A dermatoscopic image of a skin lesion.
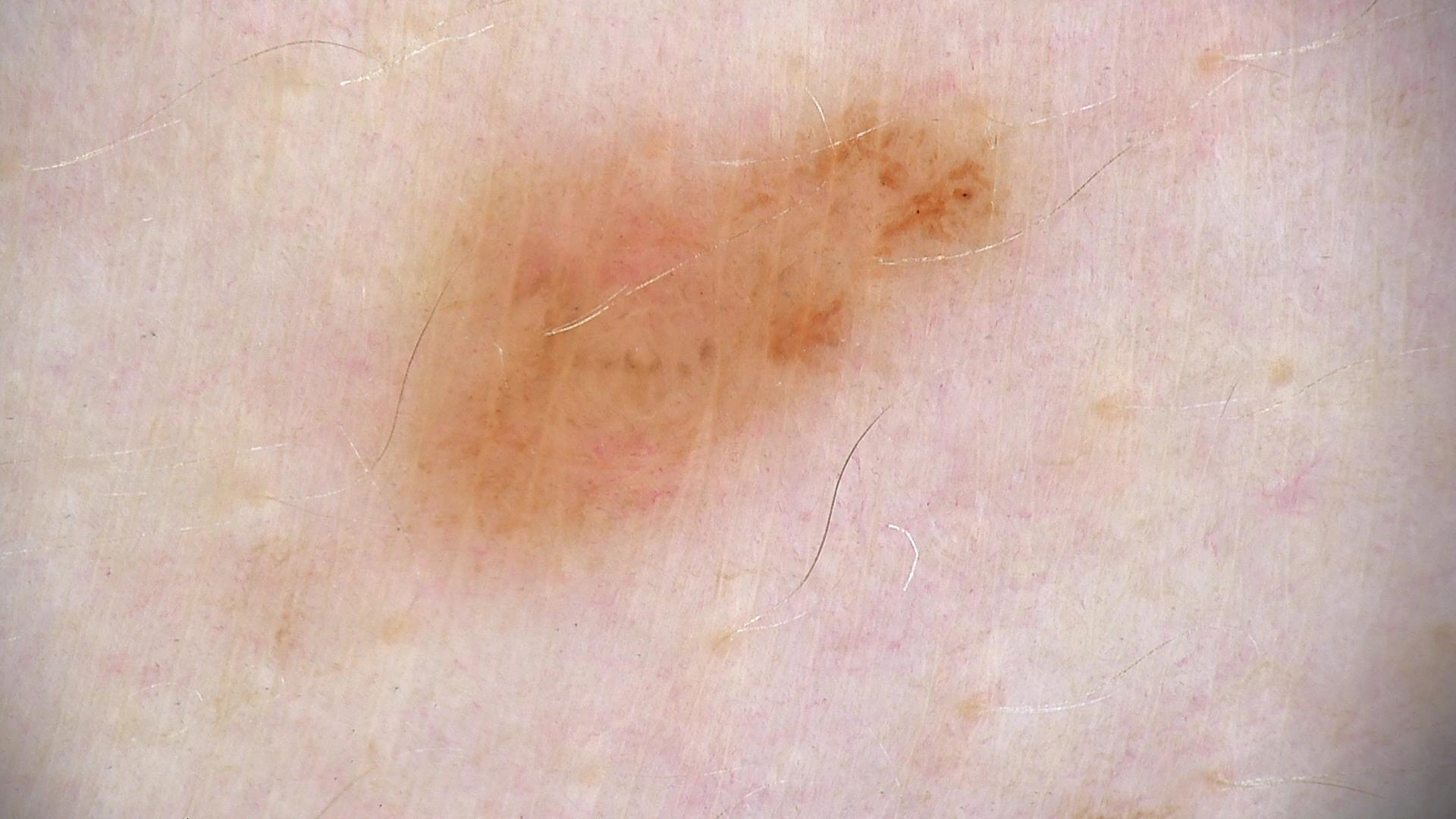label=dysplastic junctional nevus (expert consensus).